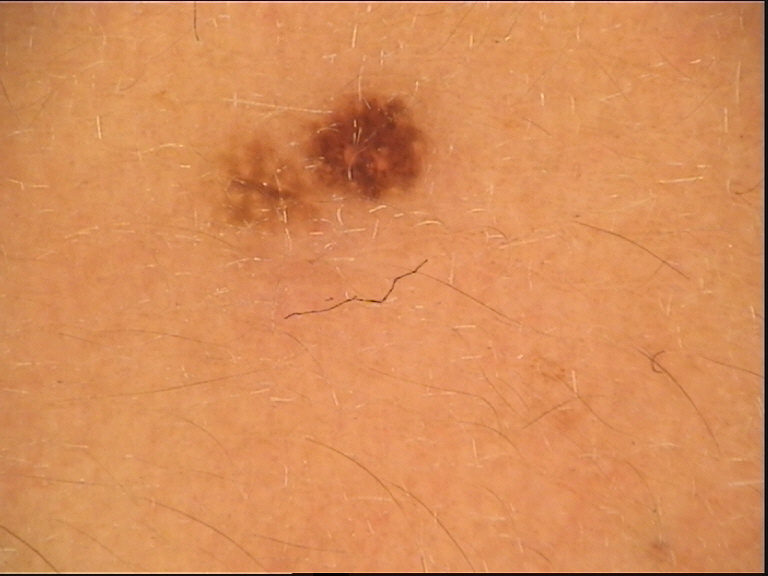image — dermatoscopy; diagnosis — dysplastic junctional nevus (expert consensus).